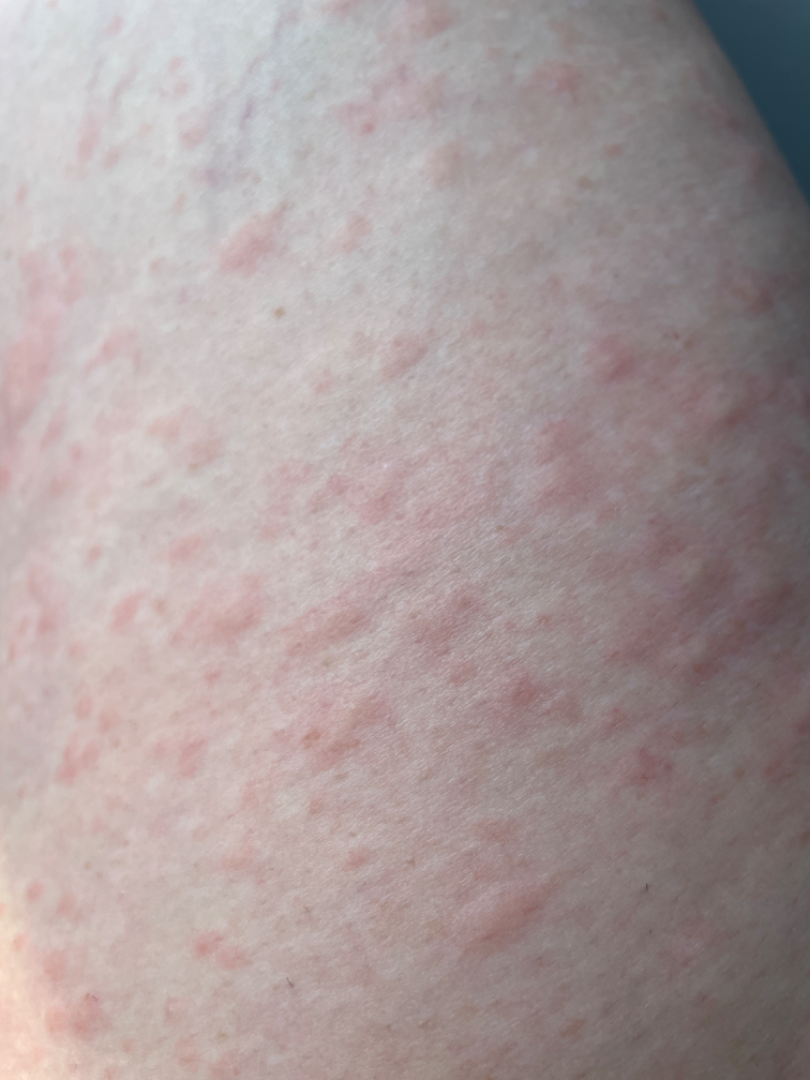The contributor is a female aged 40–49. FST I. The patient described the issue as a rash. Located on the top or side of the foot and leg. No constitutional symptoms were reported. Reported duration is about one day. The photograph is a close-up of the affected area. The lesion is associated with itching. The reviewing dermatologists' impression was: most consistent with Urticaria; less probable is Eczema; less likely is Allergic Contact Dermatitis; lower on the differential is Viral Exanthem; a remote consideration is Hypersensitivity.